A clinical photograph of a skin lesion.
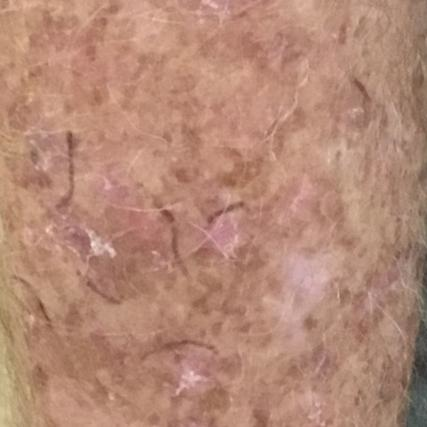Findings:
The lesion is on an arm. Per patient report, the lesion itches.
Conclusion:
Expert review favored an actinic keratosis.